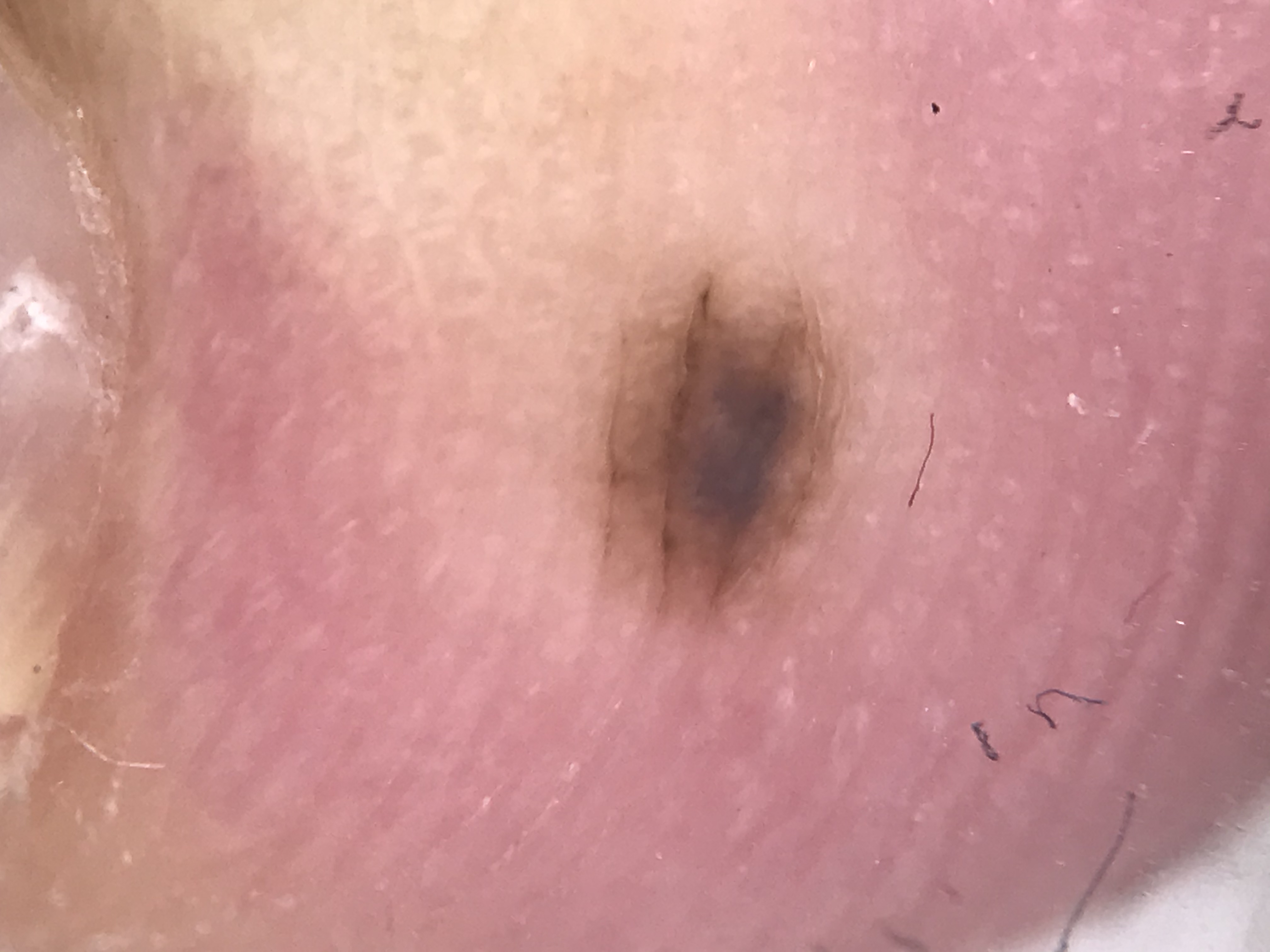The diagnostic label was an acral compound nevus.